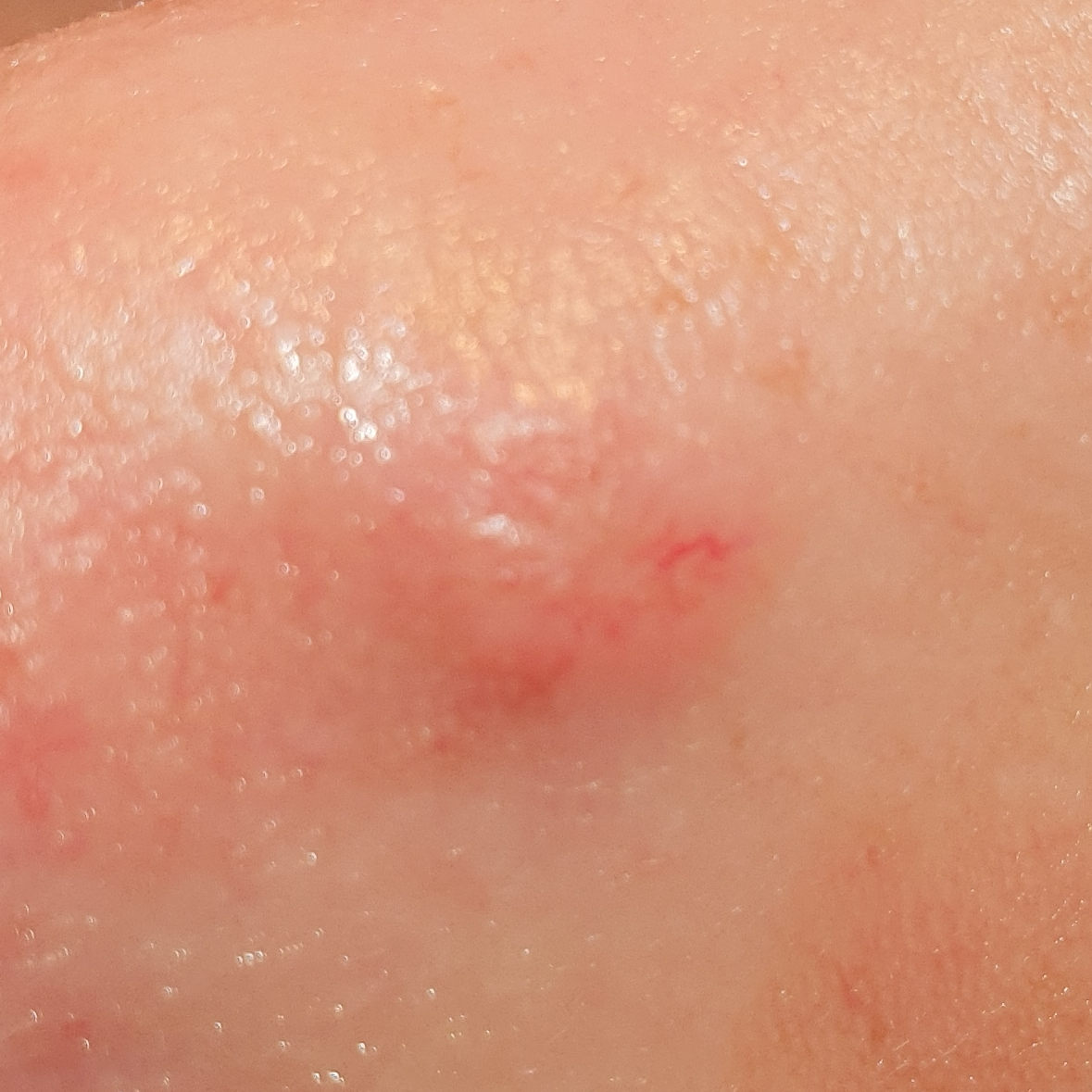History notes pesticide exposure.
A female subject in their 60s.
A clinical photograph showing a skin lesion.
Located on the nose.
Biopsy-confirmed as a basal cell carcinoma.